An image taken at a distance — 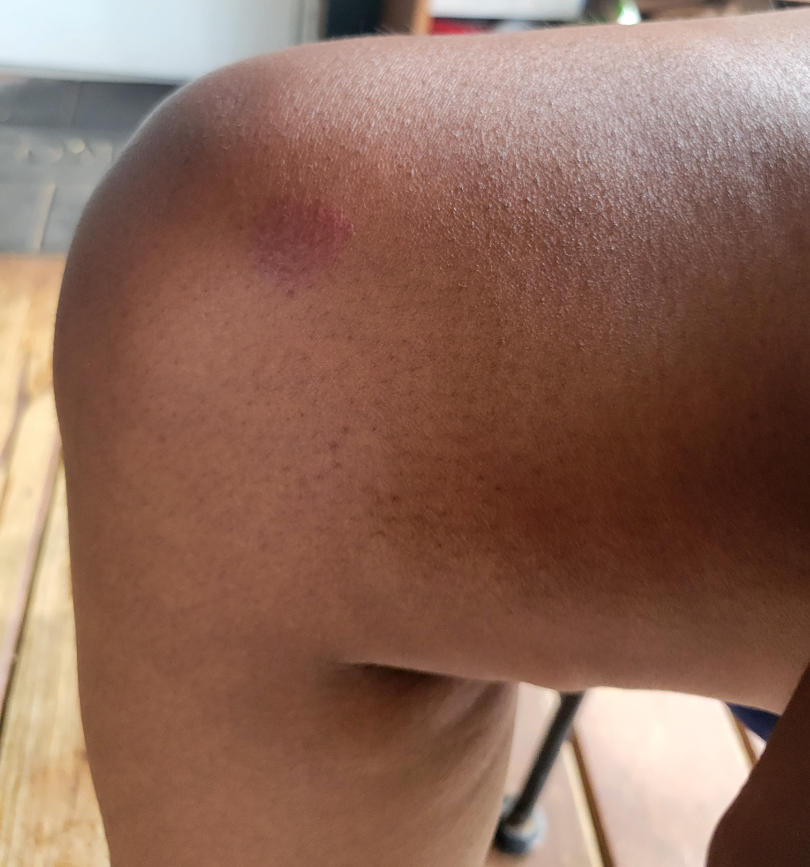The image was not sufficient for the reviewer to characterize the skin condition.